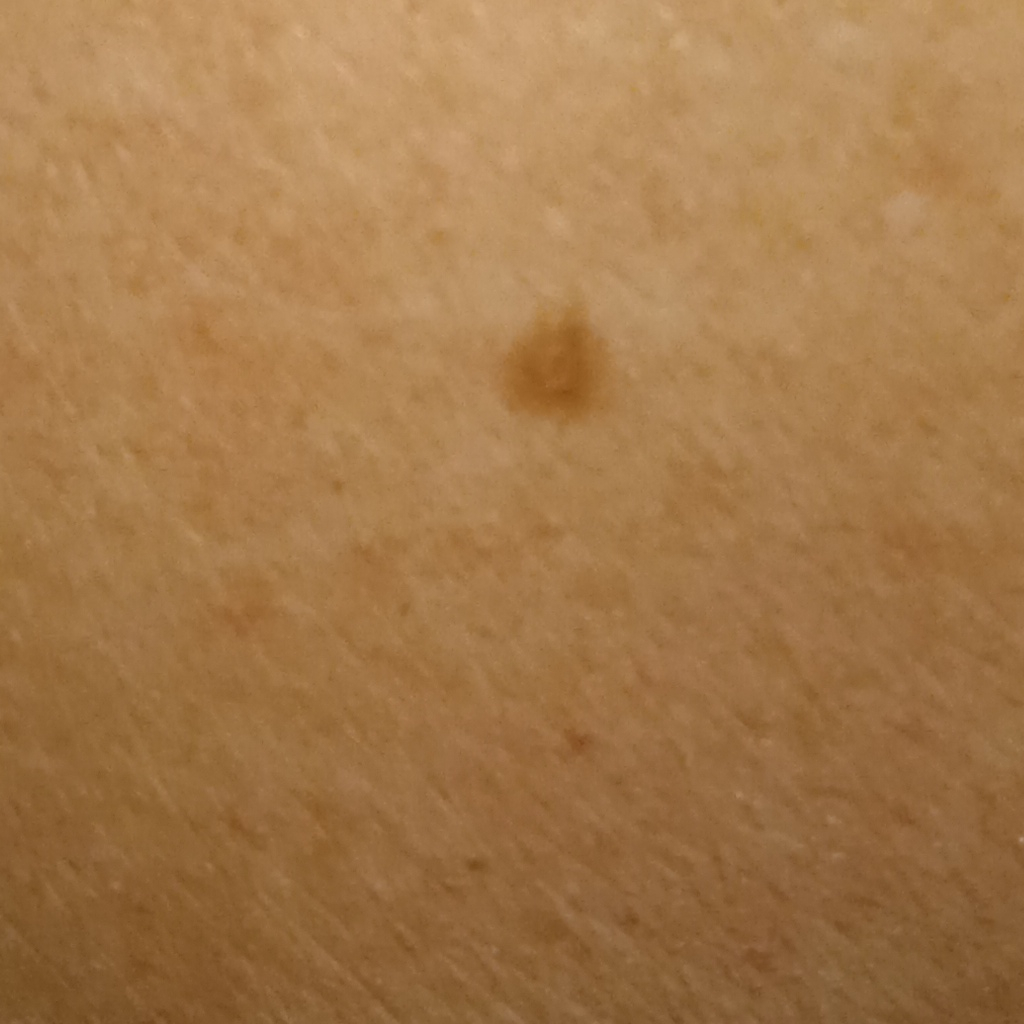A female subject 60 years of age. Acquired for a research image collection, with no referral diagnosis. A clinical photograph showing a skin lesion. Dermatologist review favored a melanocytic nevus.